Located on the top or side of the foot; female contributor, age 50–59; the photograph is a close-up of the affected area — 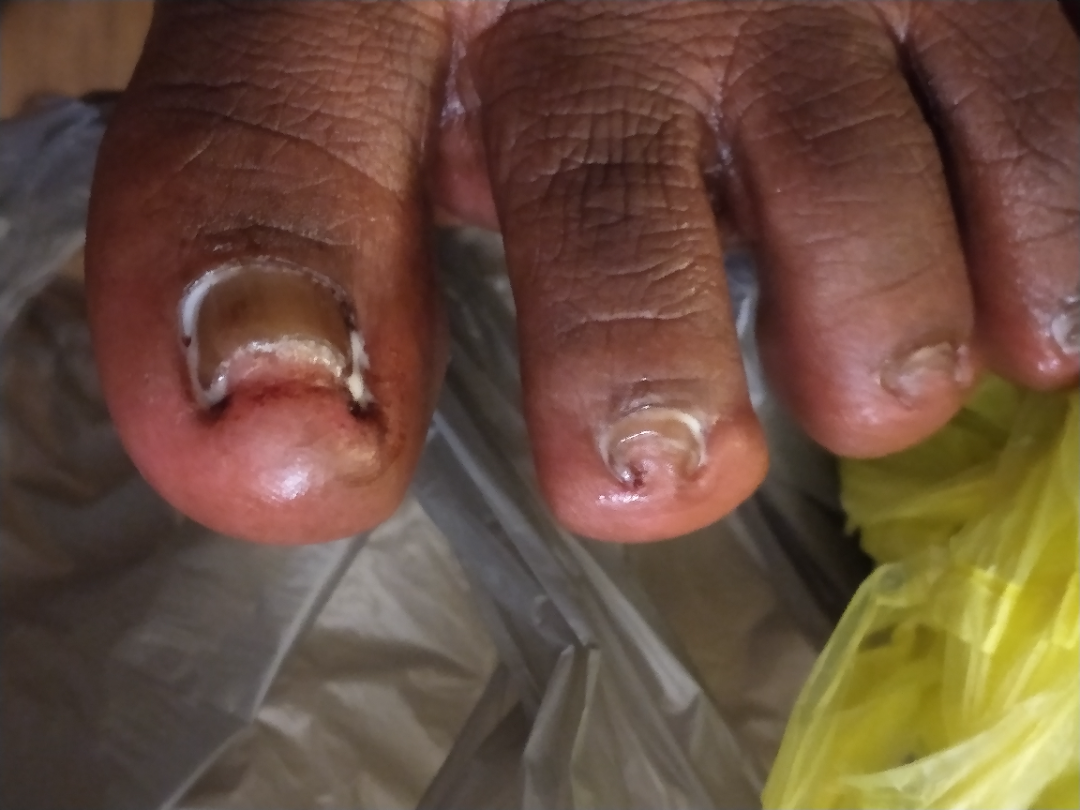Pincer nail deformity (1.00).